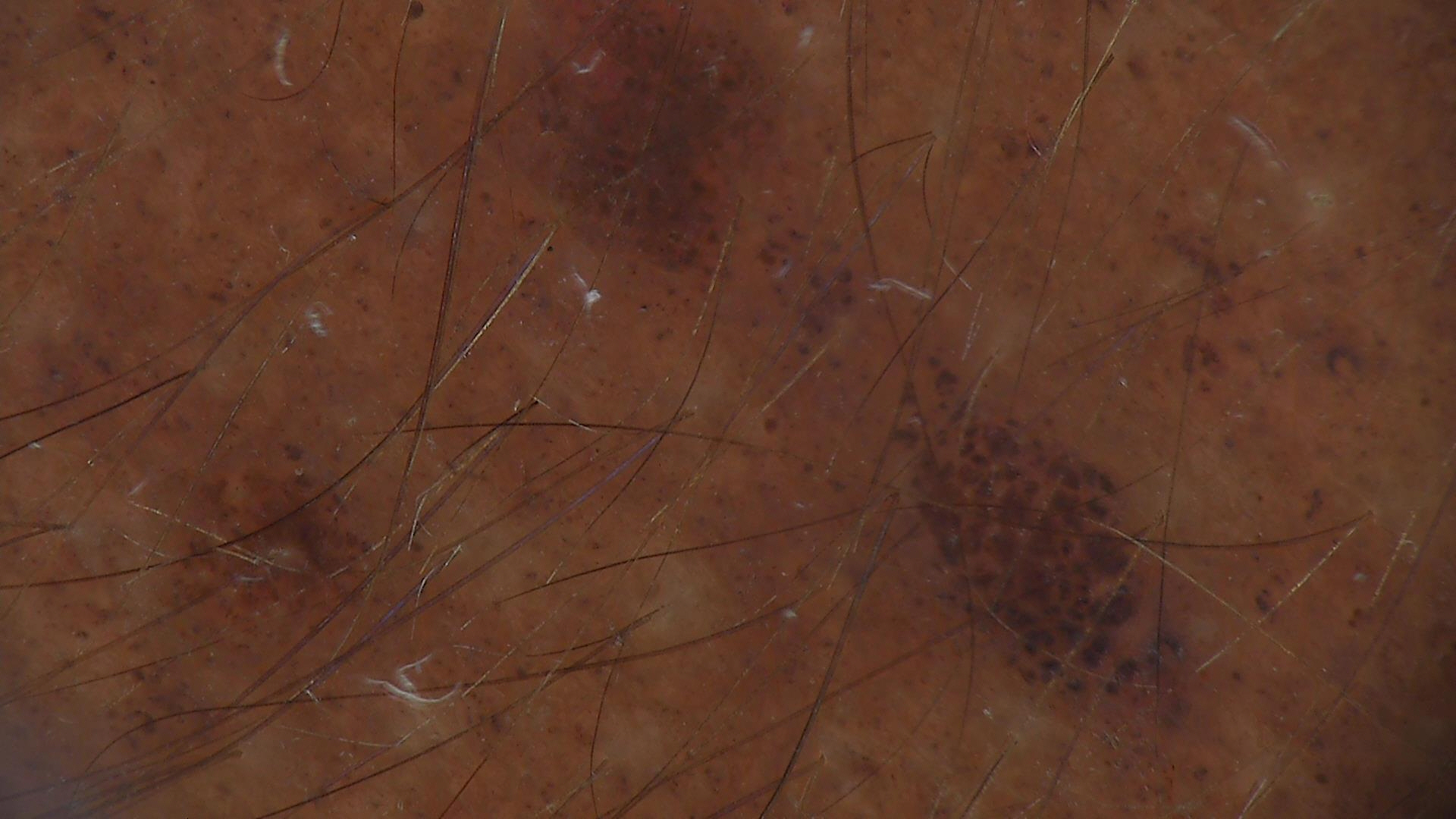* assessment — congenital compound nevus (expert consensus)